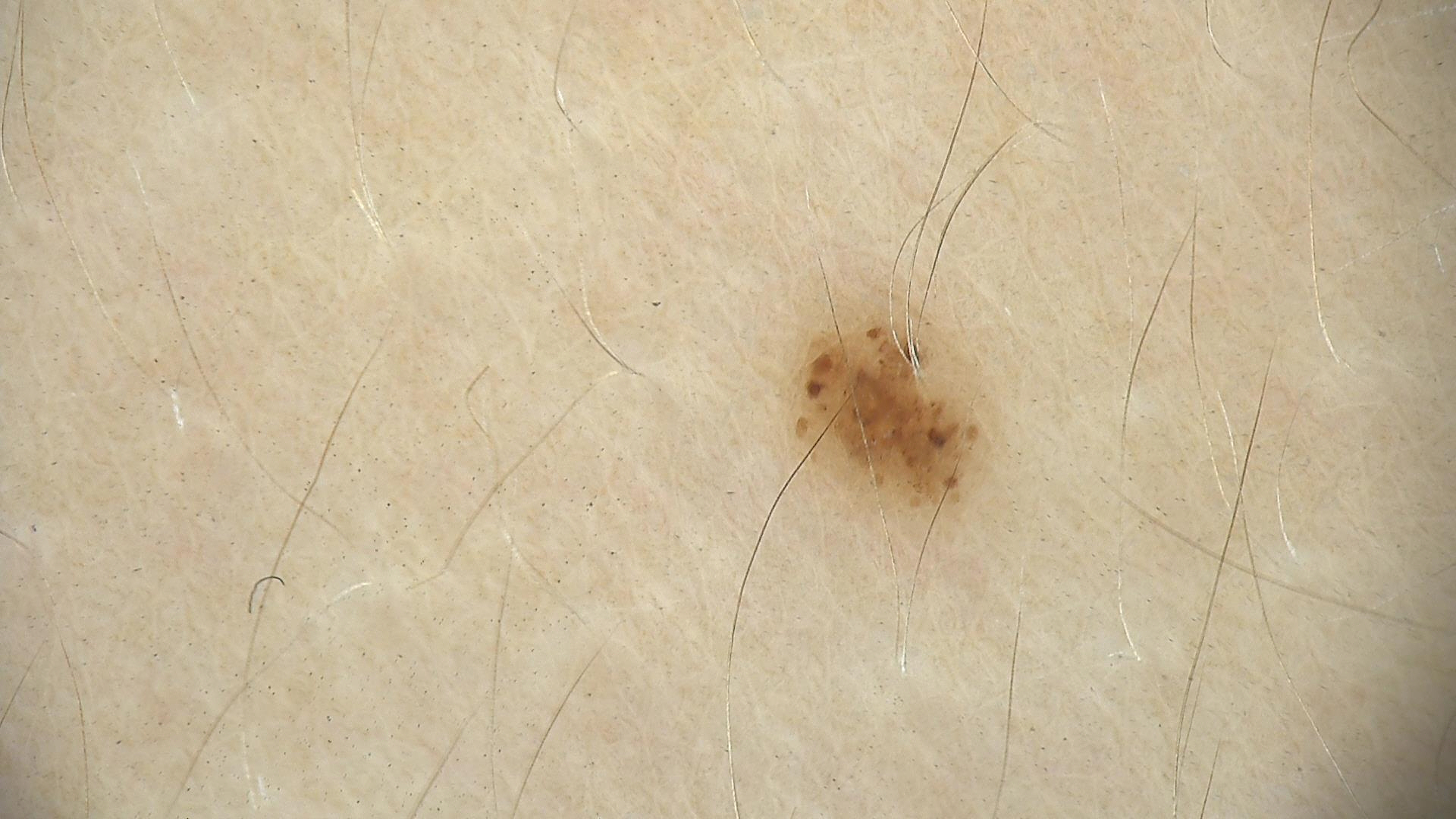diagnostic label = dysplastic junctional nevus (expert consensus).